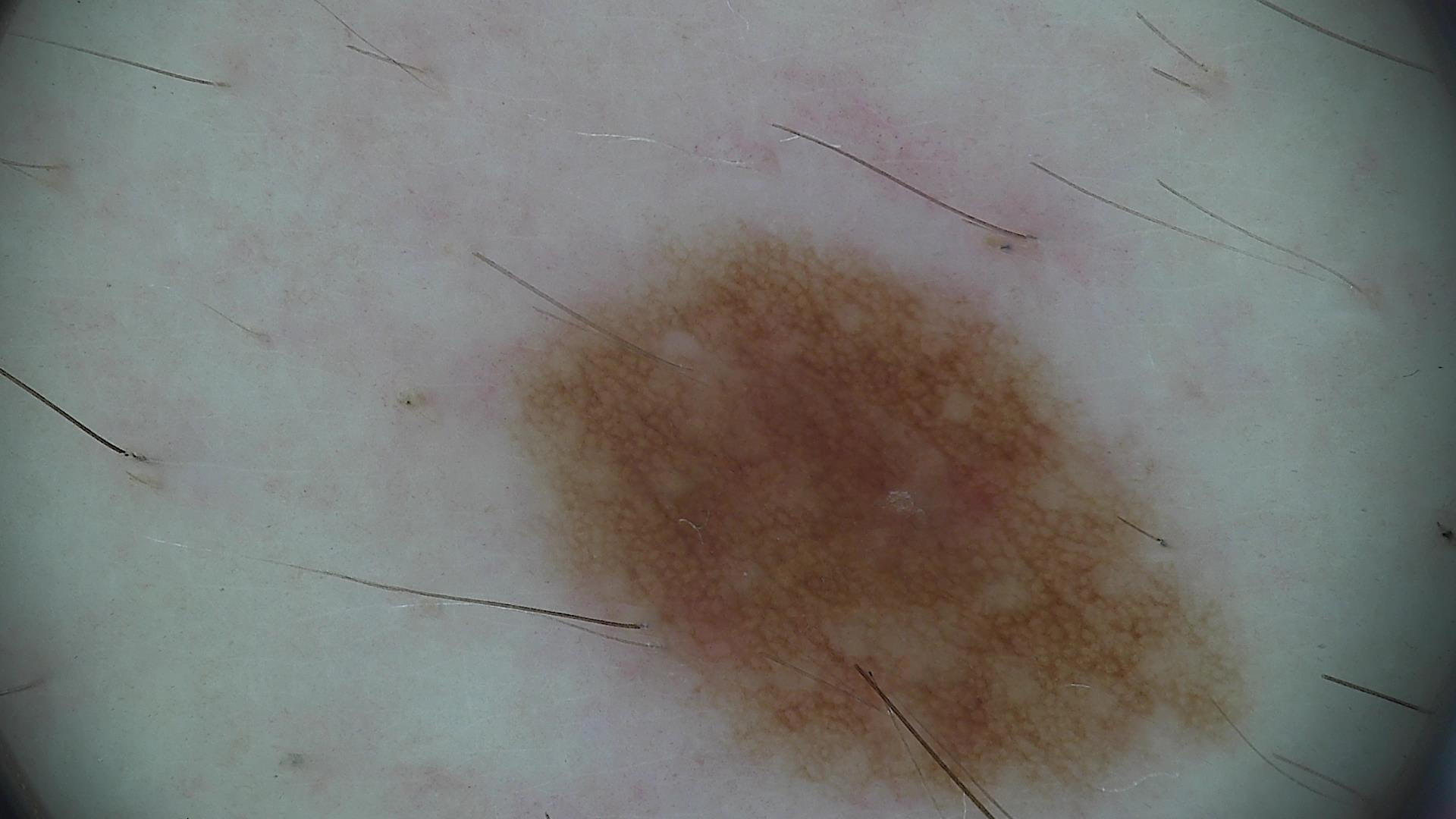A dermoscopic image of a skin lesion.
Consistent with a dysplastic junctional nevus.